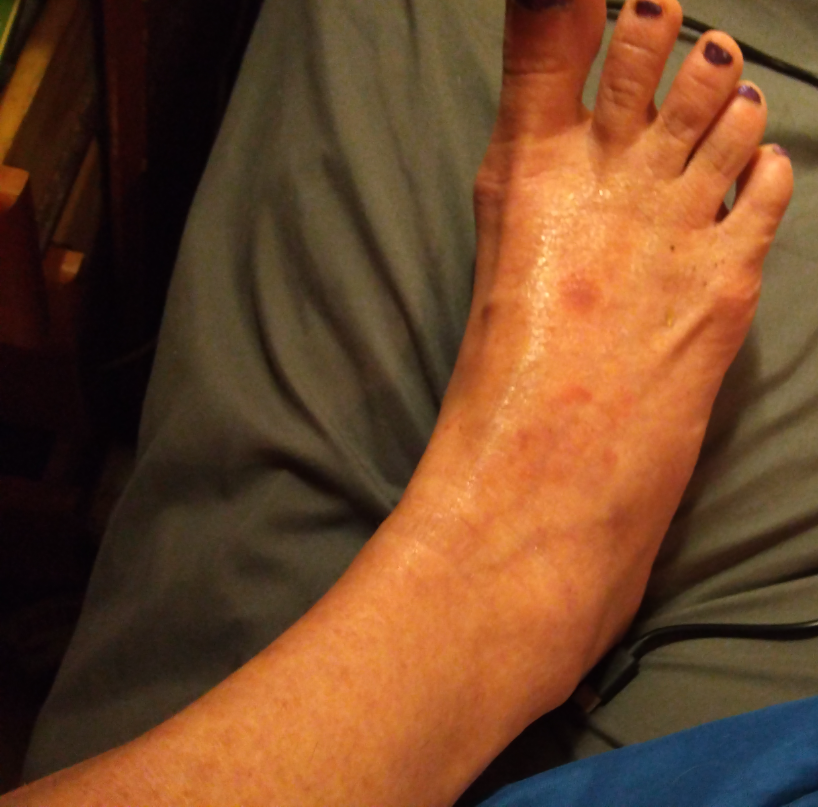Diagnostic features were not clearly distinguishable in this photograph. The lesion is described as rough or flaky. This image was taken at an angle. The leg and sole of the foot are involved. Female patient, age 50–59. The patient considered this a rash. No associated systemic symptoms reported. The lesion is associated with bothersome appearance, enlargement and itching. The patient notes the condition has been present for three to twelve months.